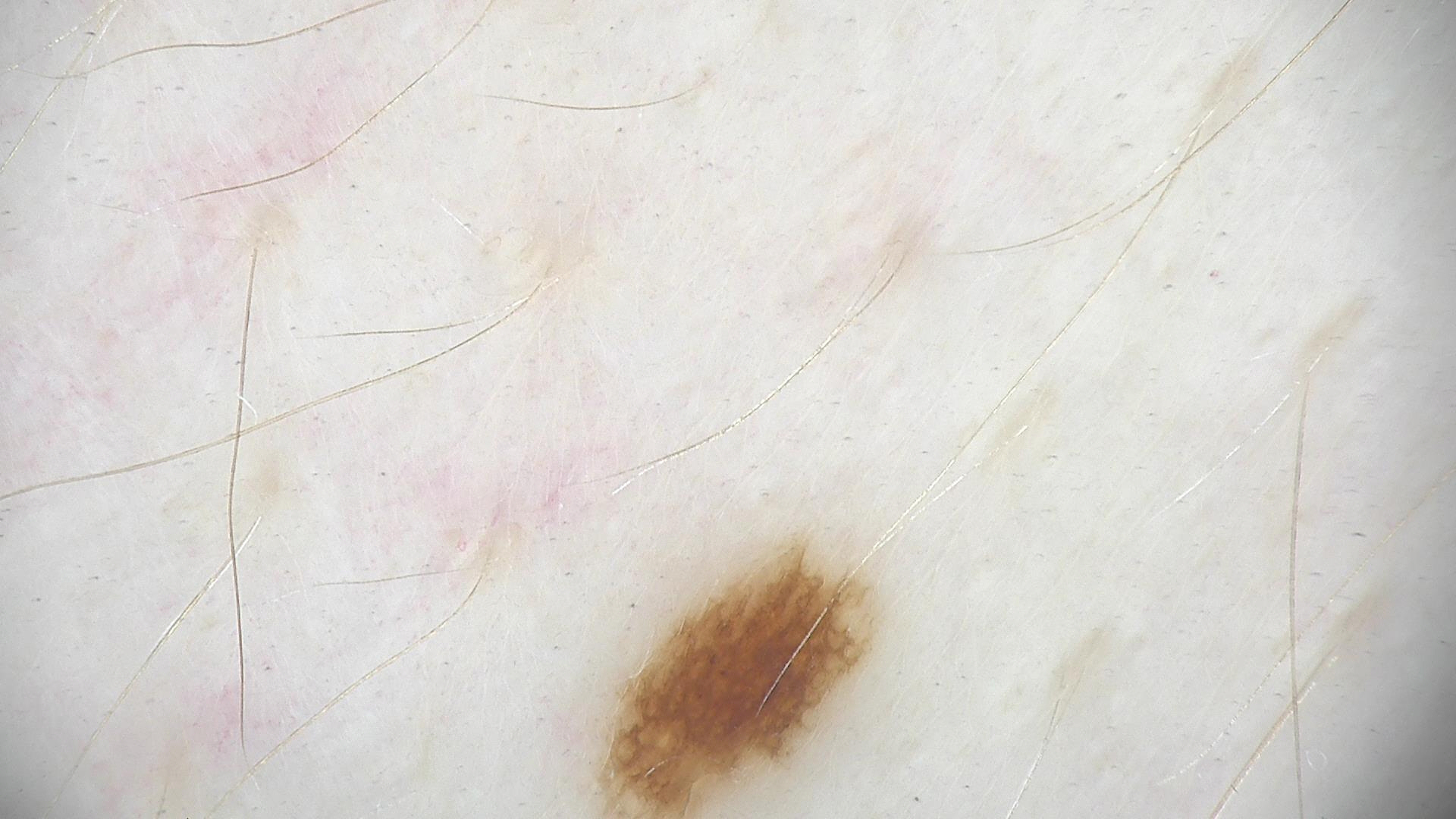A dermoscopic photograph of a skin lesion. Classified as a benign lesion — a dysplastic junctional nevus.